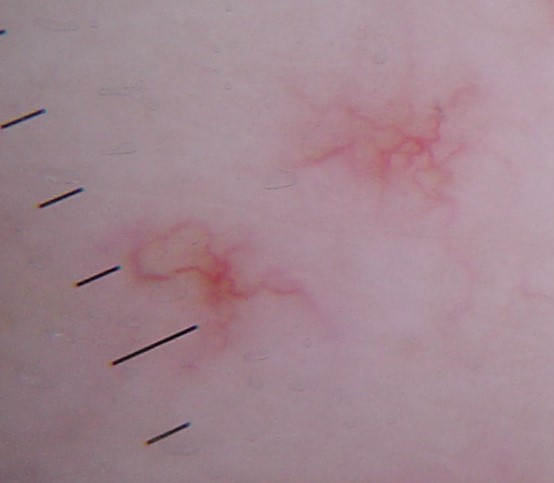The diagnosis was a spider angioma.